The affected area is the leg · female subject, age 30–39 · an image taken at a distance:
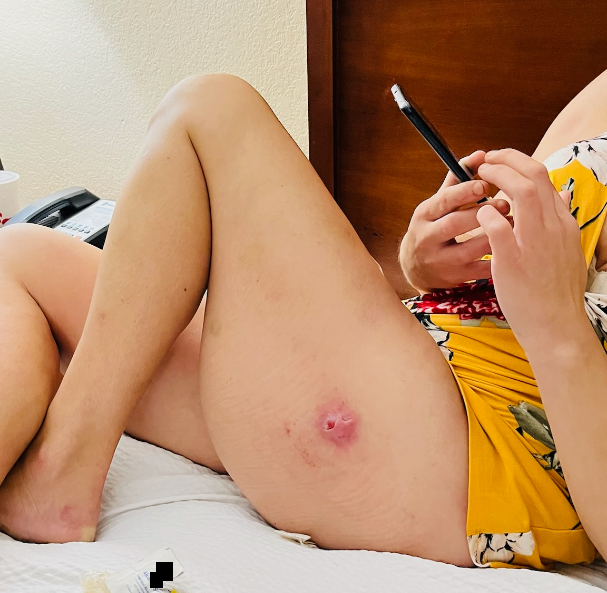Patient information:
Reported lesion symptoms include pain, itching, burning and bothersome appearance. Fitzpatrick phototype V; lay graders estimated Monk skin tone scale 1 (US pool) or 2 (India pool). The patient reports the condition has been present for three to twelve months. The lesion is described as raised or bumpy, rough or flaky and fluid-filled. Associated systemic symptoms include chills, joint pain, shortness of breath and fatigue.
Review:
On remote dermatologist review: the impression is Hidradenitis.